A dermoscopic close-up of a skin lesion · the patient is a female in their mid-40s.
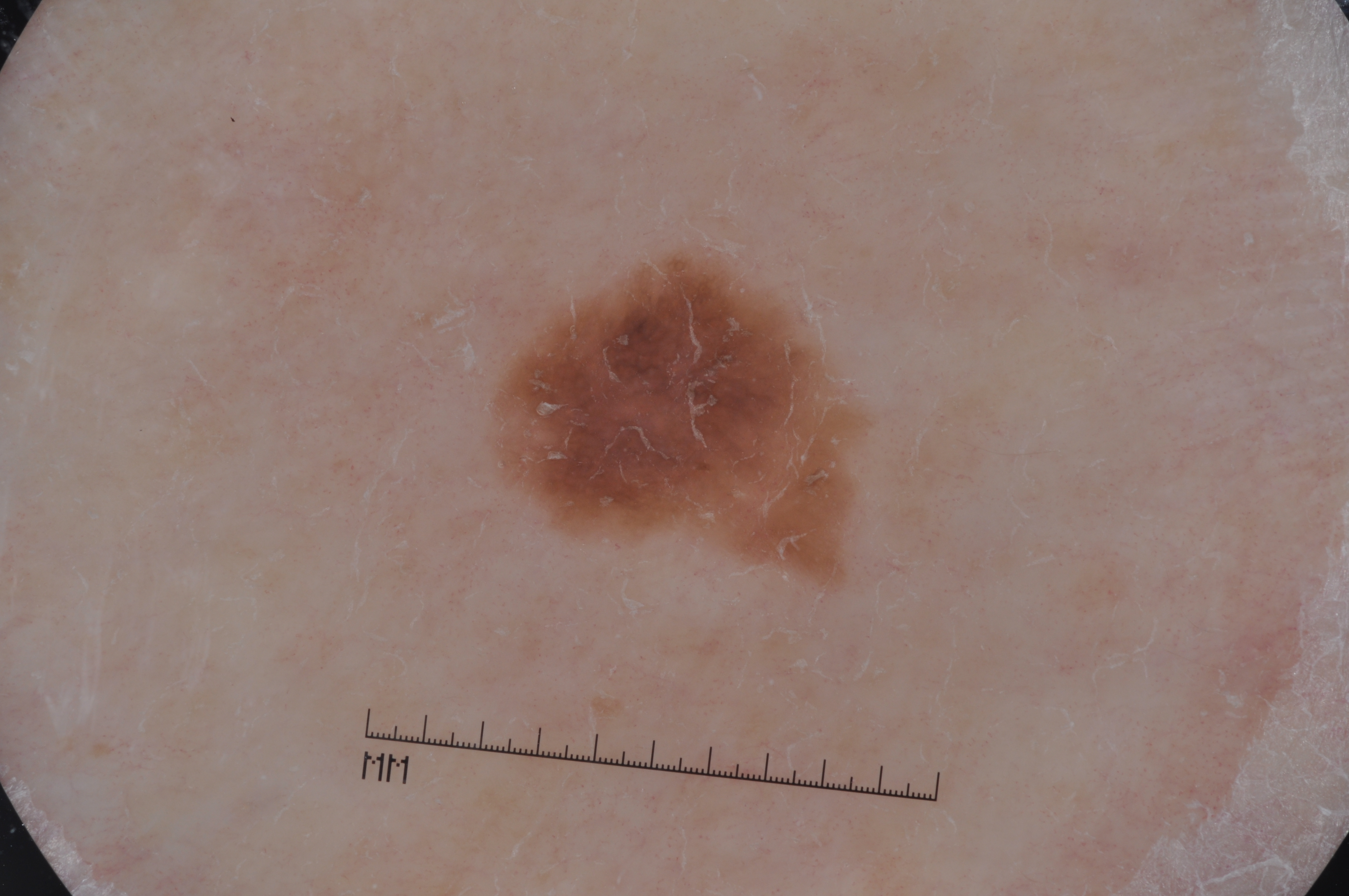In (x1, y1, x2, y2) order, the lesion's extent is 495 259 854 574.
The dermoscopic pattern shows pigment network.
A small lesion within a wider field of skin.
The diagnostic assessment was a melanocytic nevus, a benign skin lesion.